The patient says their skin tans without first burning; a skin lesion imaged with a dermatoscope; numerous moles by the patient's own estimate; imaged for a research study, with no referral diagnosis recorded; a female patient aged 78; by self-report, no sunbed use: 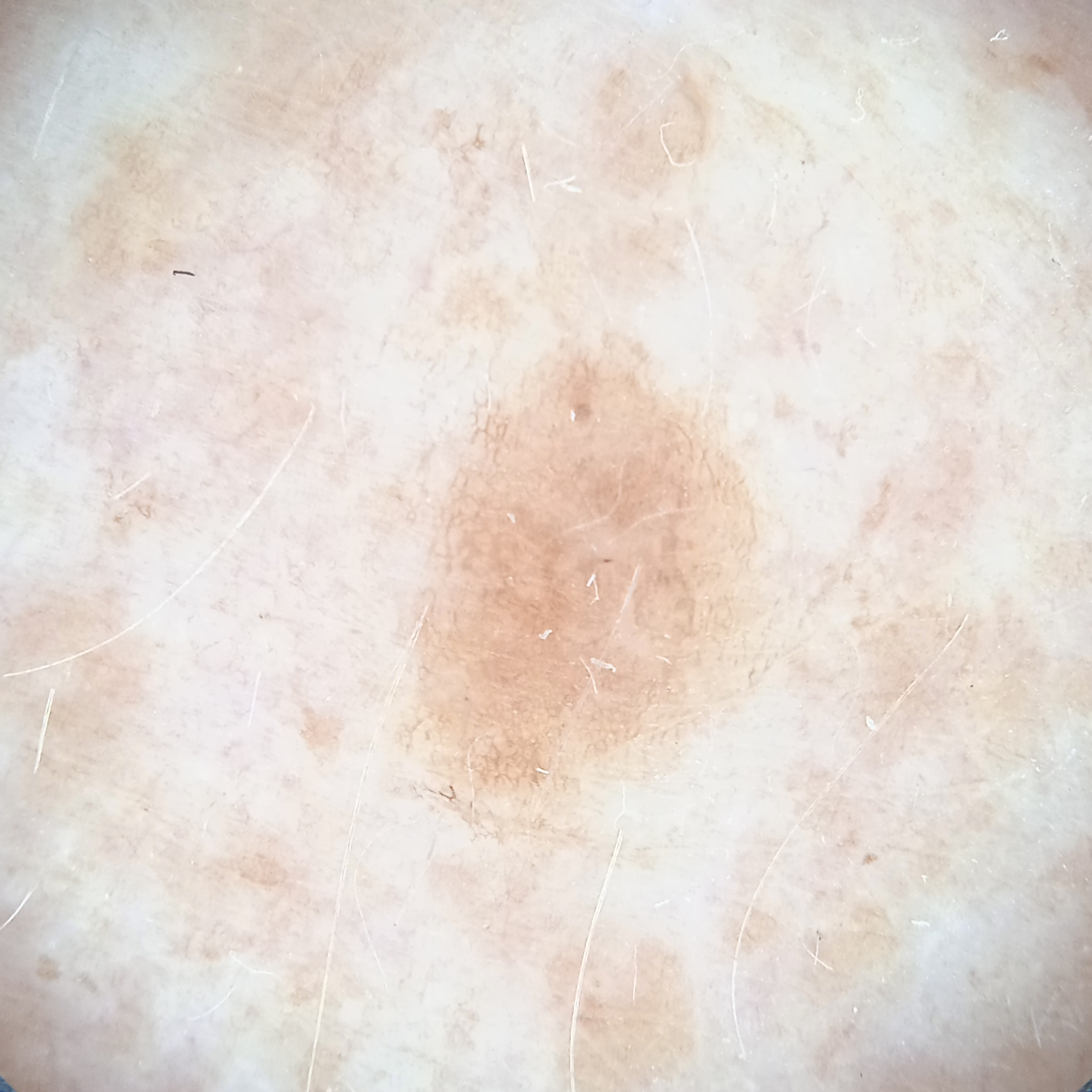{"lesion_location": "an arm", "lesion_size": {"diameter_mm": 5.3}, "diagnosis": {"name": "seborrheic keratosis", "malignancy": "benign"}}